A dermoscopic image of a skin lesion.
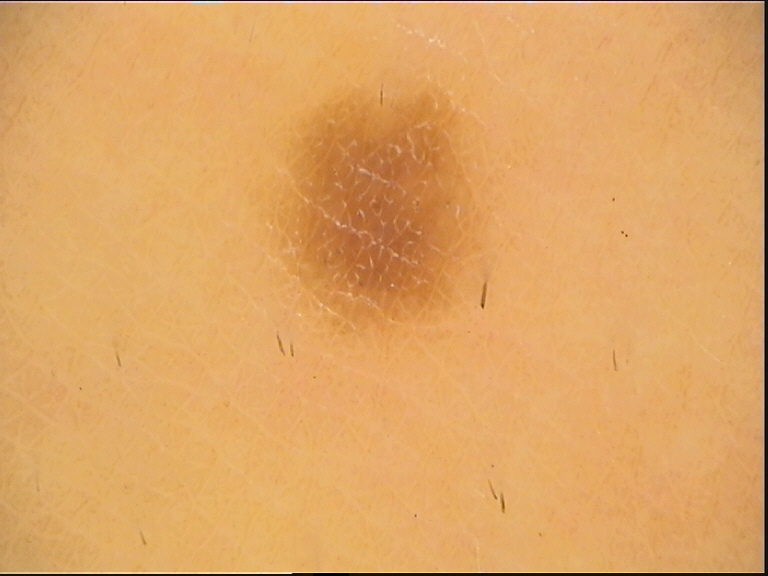Q: What kind of lesion is this?
A: keratinocytic
Q: What is this lesion?
A: seborrheic keratosis (expert consensus)